The photograph is a close-up of the affected area — 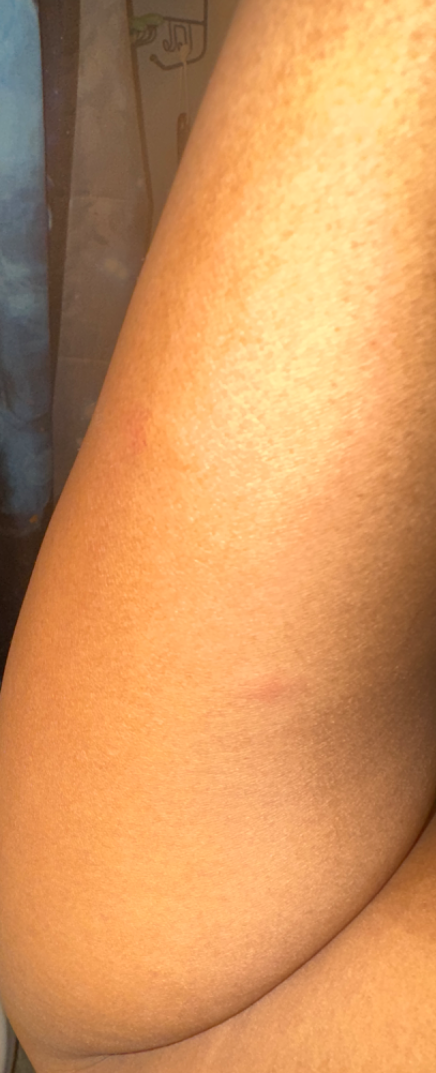On teledermatology review: most likely Urticaria; also raised was Allergic Contact Dermatitis.